A dermoscopic photograph of a skin lesion.
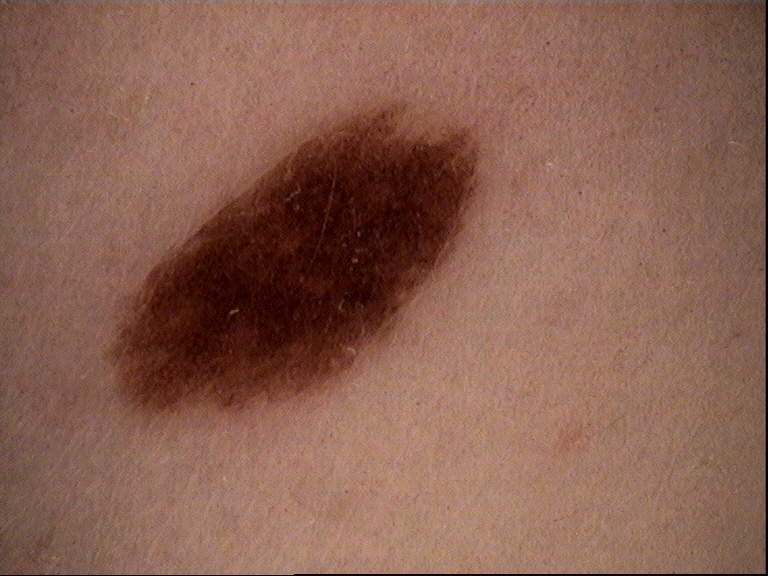label: dysplastic junctional nevus (expert consensus).